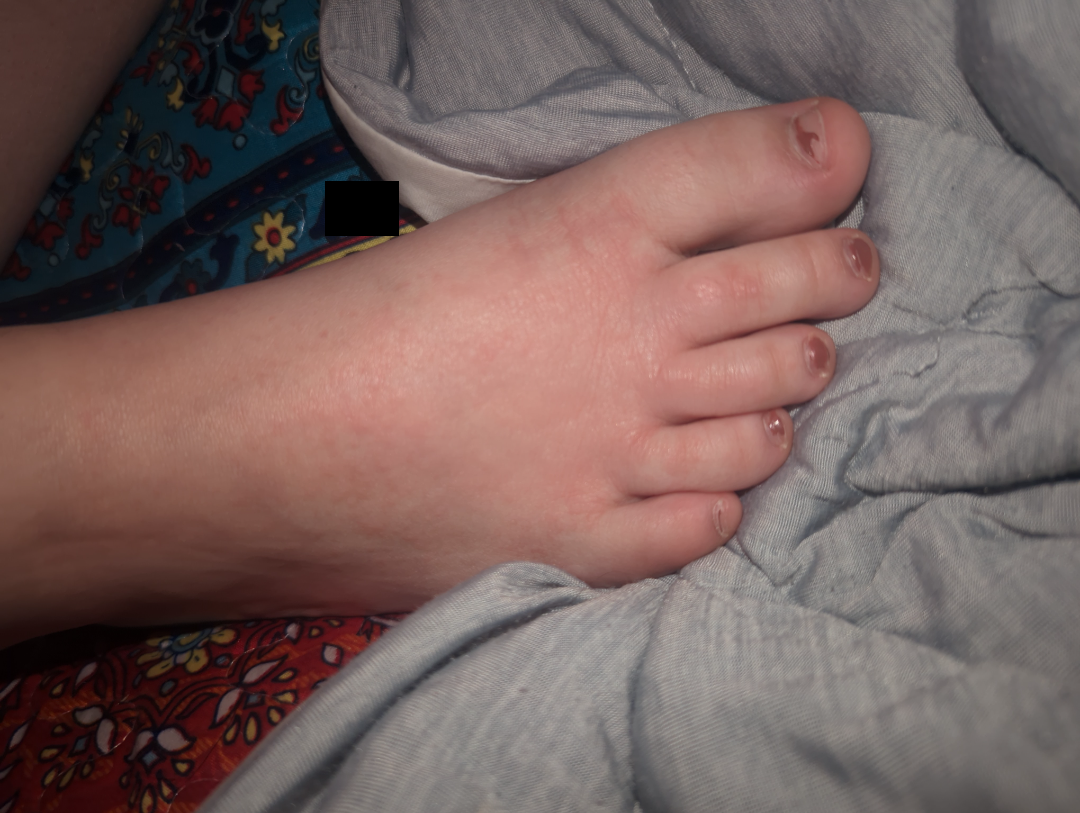The dermatologist could not determine a likely condition from the photograph alone.
This is a close-up image.
The contributor is female.
The affected area is the arm and top or side of the foot.
Reported duration is about one day.
The patient reports burning, bothersome appearance, enlargement and itching.
Self-categorized by the patient as a rash.